The patient also reports joint pain and fatigue. Symptoms reported: bothersome appearance. A close-up photograph. Female contributor, age 50–59. The lesion is described as flat. Present for three to twelve months. Located on the arm: 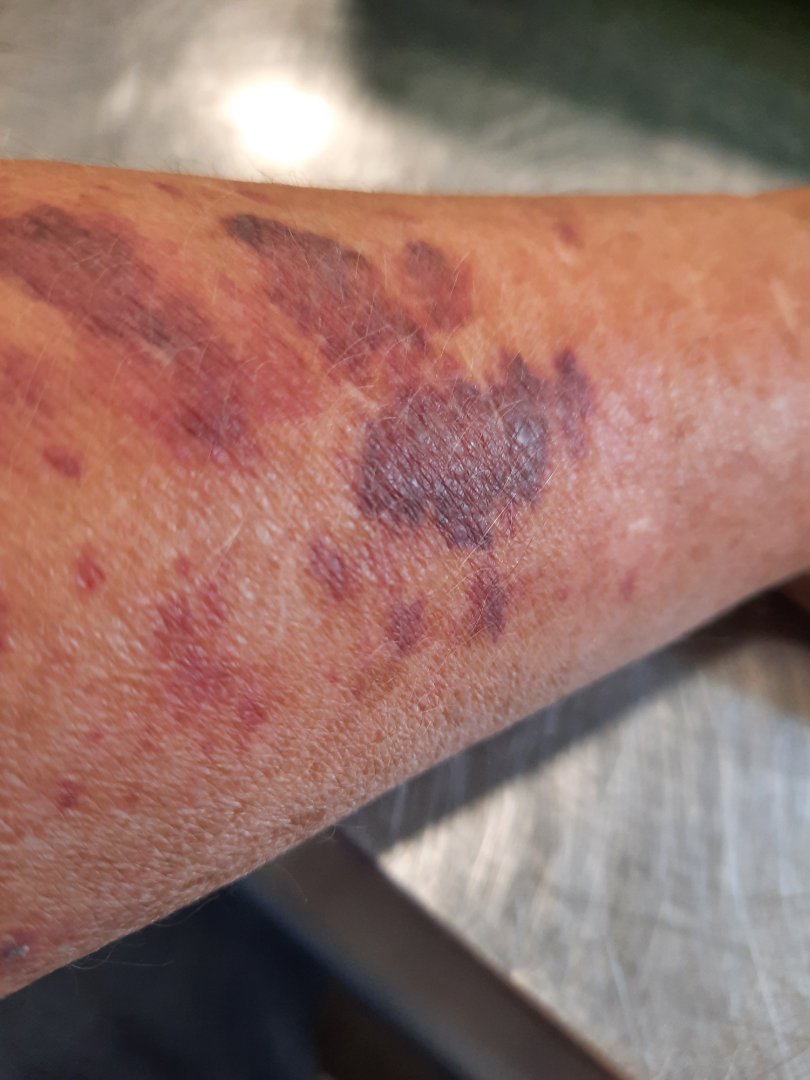clinical impression=favoring ecchymoses; also consider Kaposi's sarcoma of skin; with consideration of Leukocytoclastic Vasculitis